Acquired for a research image collection, with no referral diagnosis. A dermoscopy image of a skin lesion. A female patient 26 years old. The patient reports a history of sunbed use and no immunosuppression. The patient describes having numerous moles: 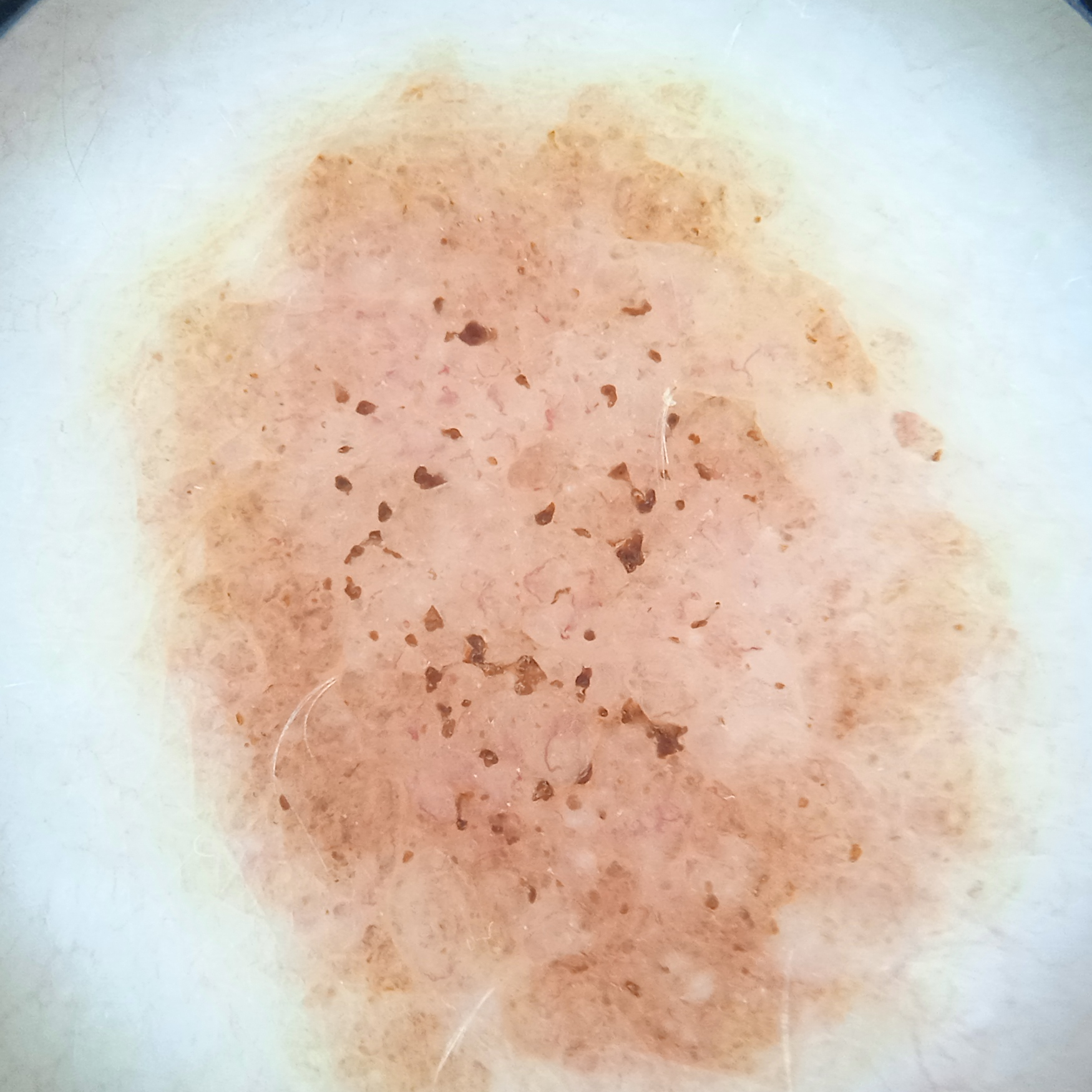Q: Where is the lesion?
A: the torso
Q: Lesion size?
A: 13 mm
Q: What was the diagnosis?
A: melanocytic nevus (dermatologist consensus)